A clinical photograph of a skin lesion; by self-report, a personal history of cancer, no personal history of skin cancer, and no family history of skin cancer; the patient describes having numerous moles; a male patient age 73.
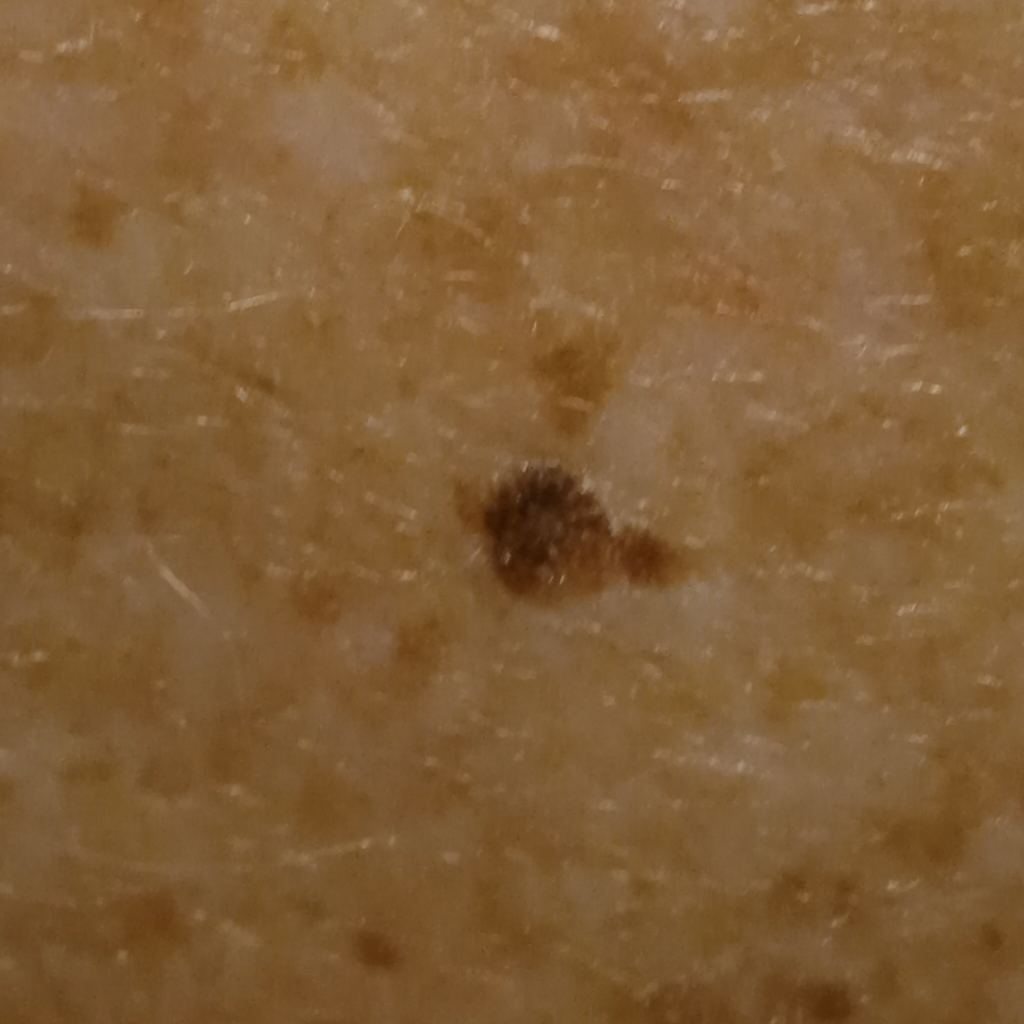Findings: The lesion measures approximately 5.5 mm. Conclusion: The diagnostic impression was a seborrheic keratosis.